The palm and back of the hand are involved · the contributor reports the condition has been present for one to three months · the contributor is 60–69, female · this is a close-up image · the contributor reports the lesion is rough or flaky · the contributor reports burning and itching · self-categorized by the patient as a rash:
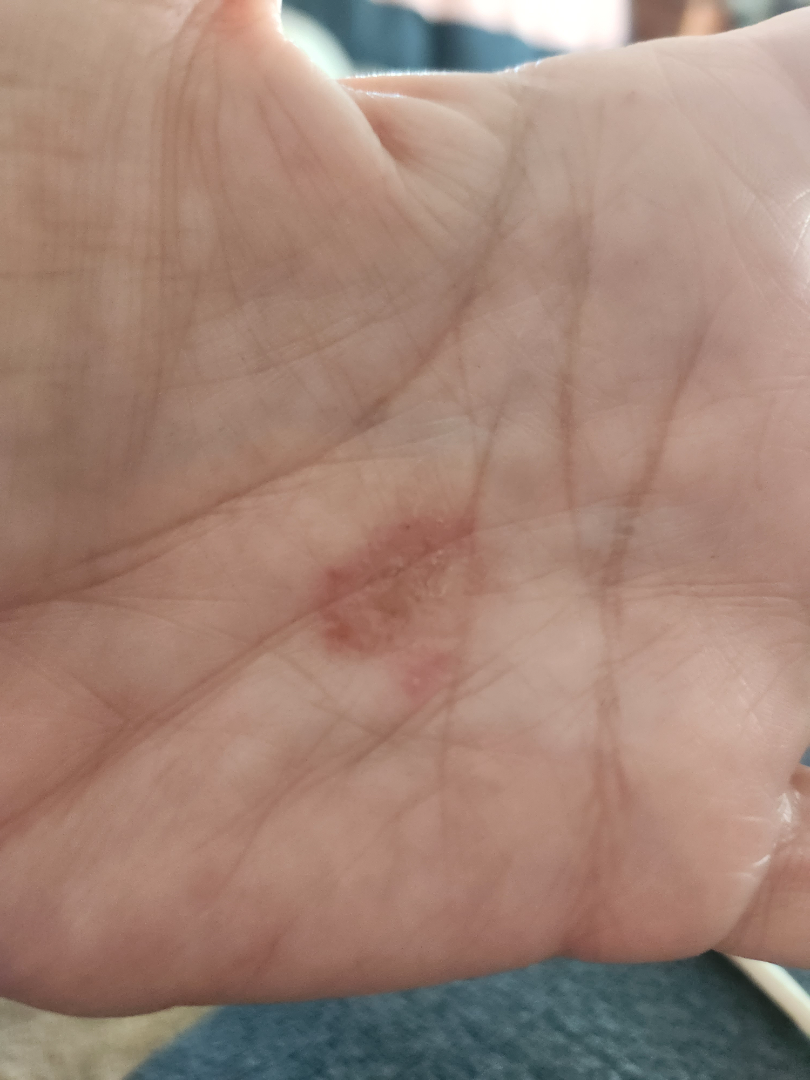Single-reviewer assessment: the differential is split between Psoriasis and Superficial wound of body region; less likely is Allergic Contact Dermatitis.